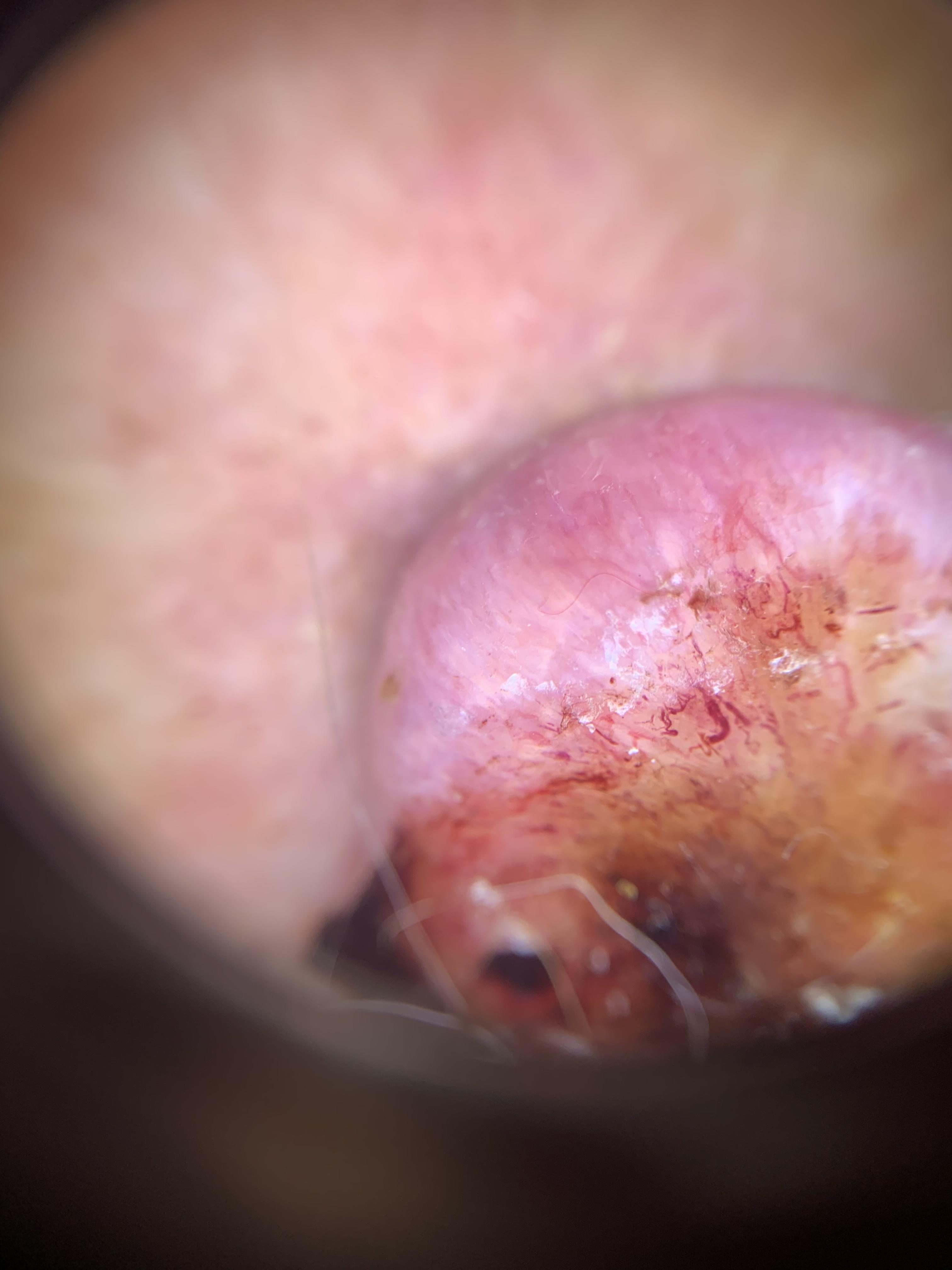A female patient in their mid- to late 80s or older.
A skin lesion imaged with a dermatoscope.
Histopathologically confirmed as a squamous cell carcinoma.